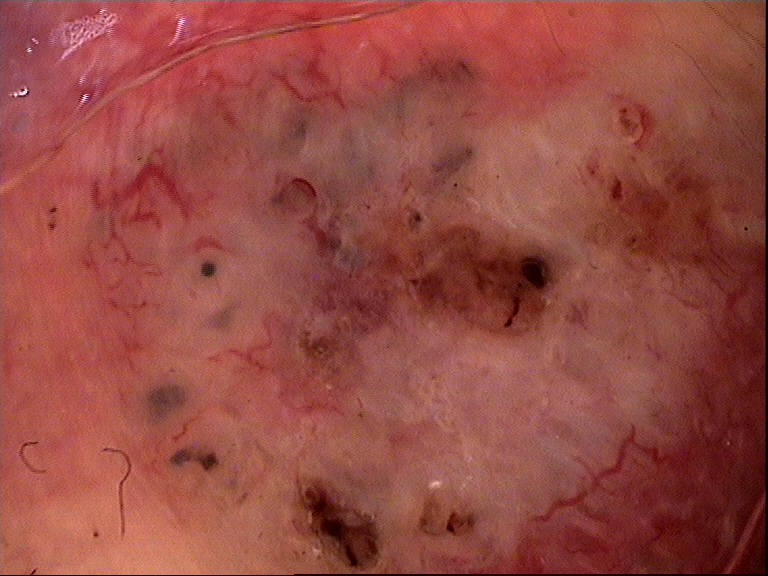<lesion>
<diagnosis>
<name>basal cell carcinoma</name>
<code>bcc</code>
<malignancy>malignant</malignancy>
<super_class>non-melanocytic</super_class>
<confirmation>histopathology</confirmation>
</diagnosis>
</lesion>